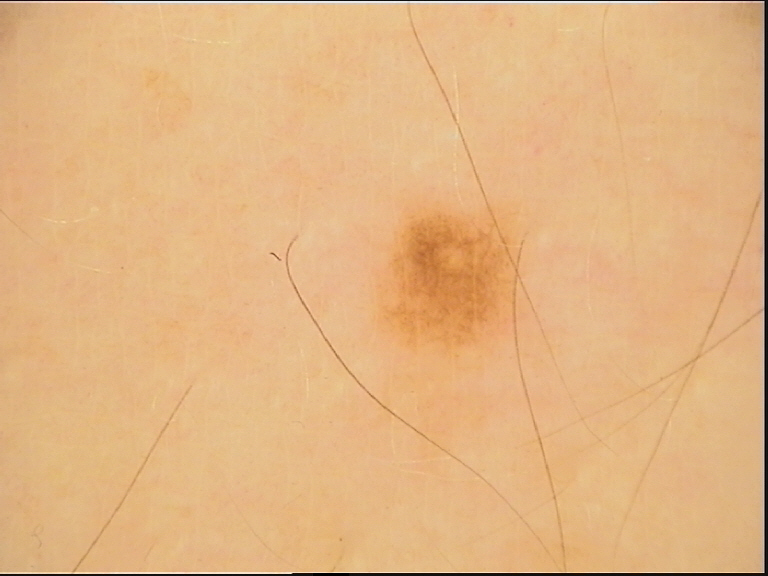The diagnostic label was a junctional nevus.